The chart records prior malignancy (patient or family) and alcohol use; the patient was assessed as Fitzpatrick III; a smartphone photograph of a skin lesion — 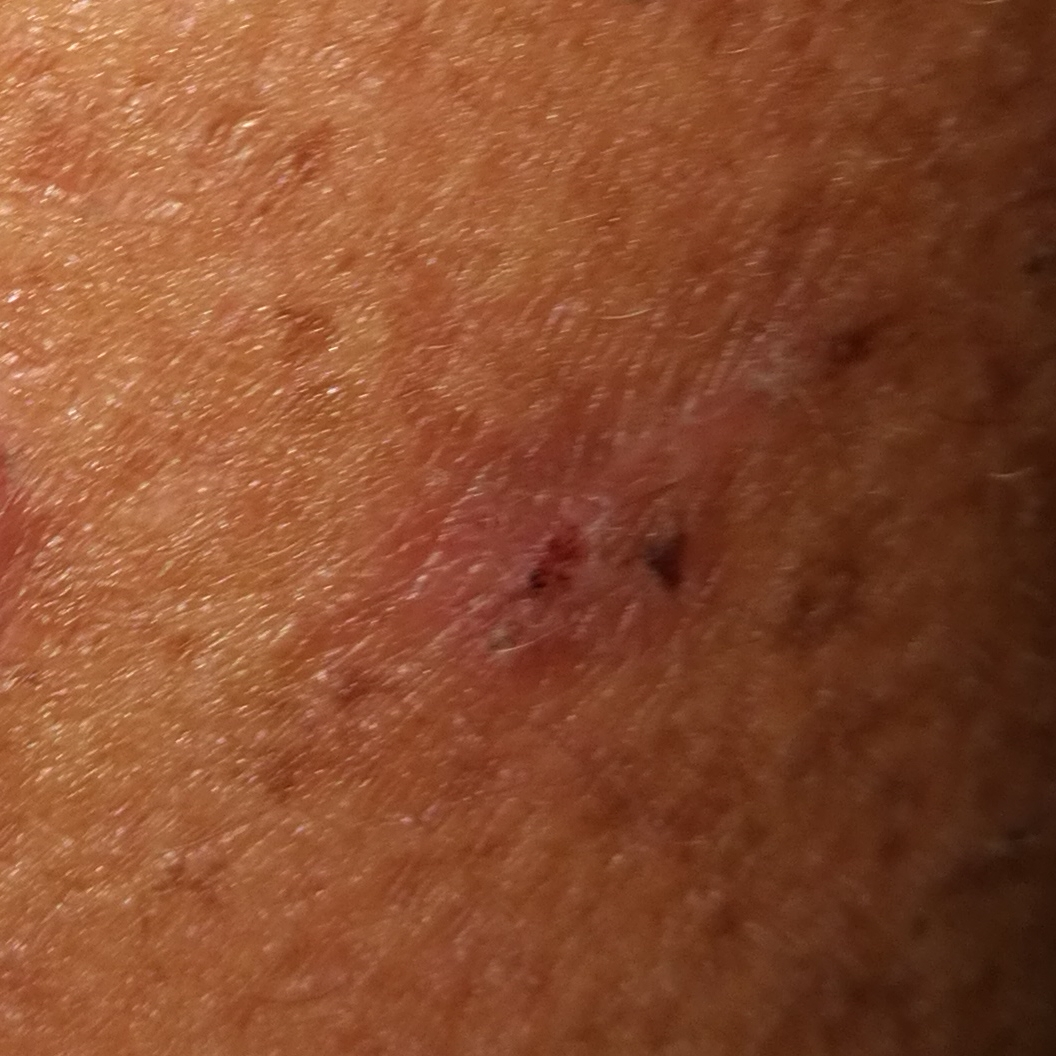Case summary: Per patient report, the lesion has grown, itches, and has bled, but is not elevated. Impression: Consistent with a lesion of indeterminate malignant potential — an actinic keratosis.